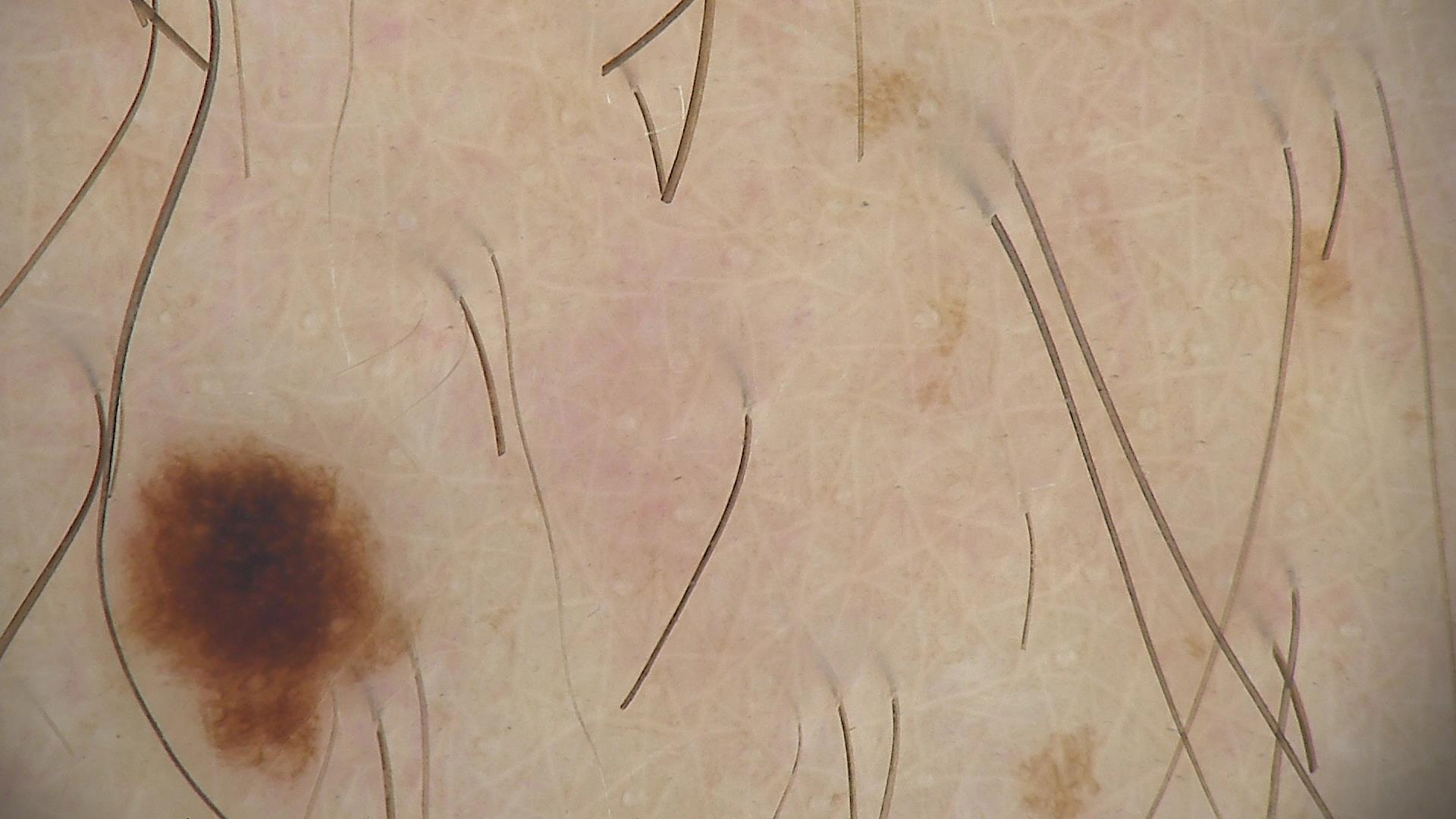A dermatoscopic image of a skin lesion. The diagnosis was a benign lesion — a dysplastic junctional nevus.